The back of the torso is involved; this is a close-up image; the contributor is 18–29, female: 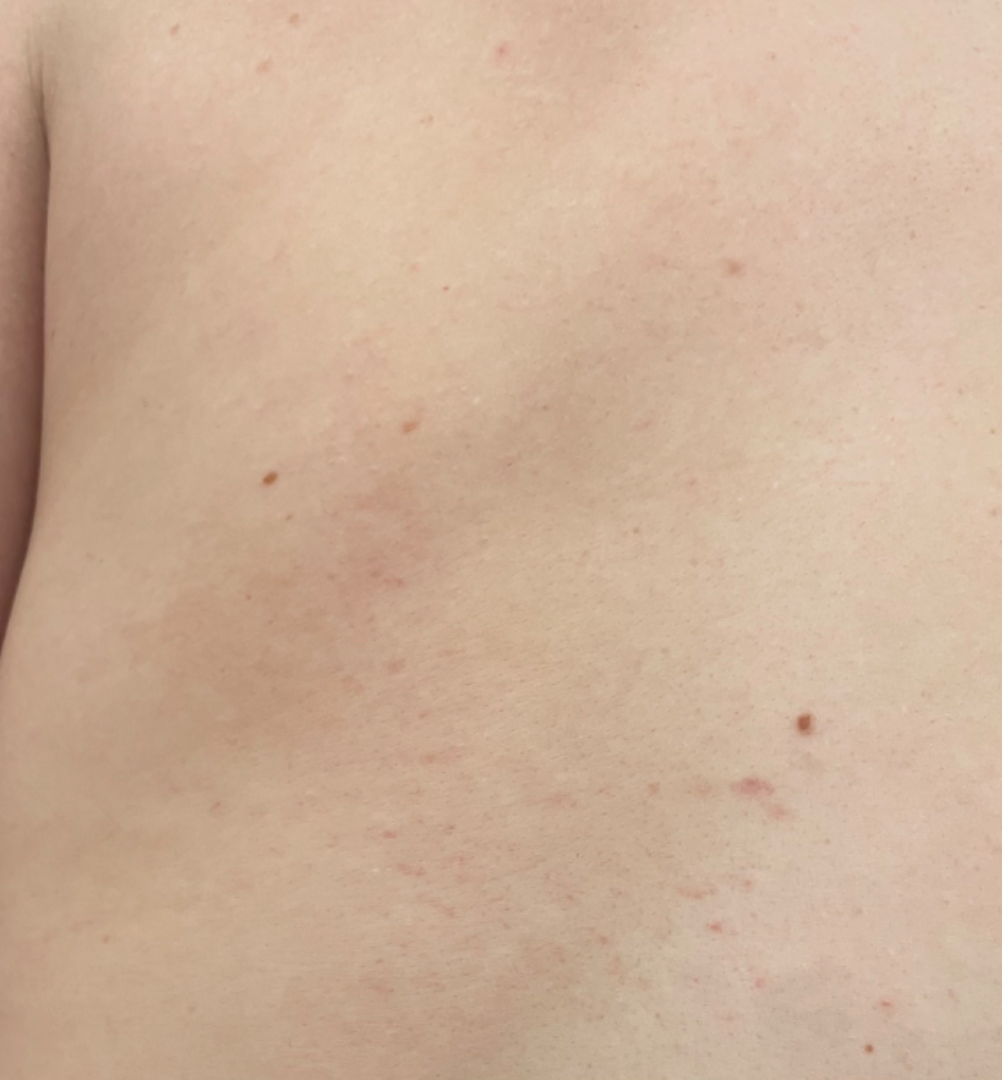Assessment: No discernible skin pathology was identified on dermatologist review.